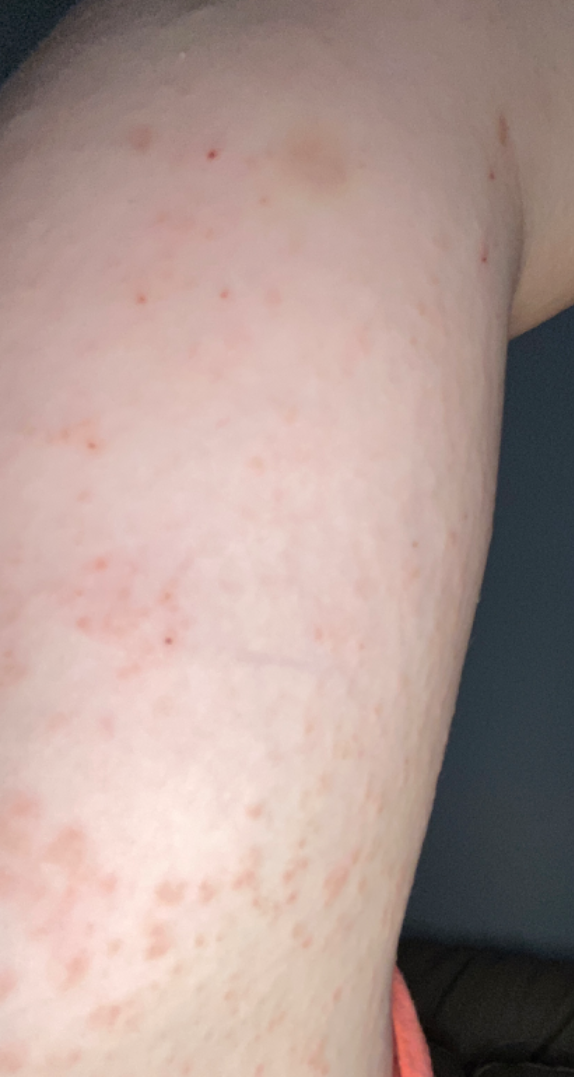clinical impression: Contact dermatitis, NOS (leading); Eczema (considered); Keratosis pilaris (remote)